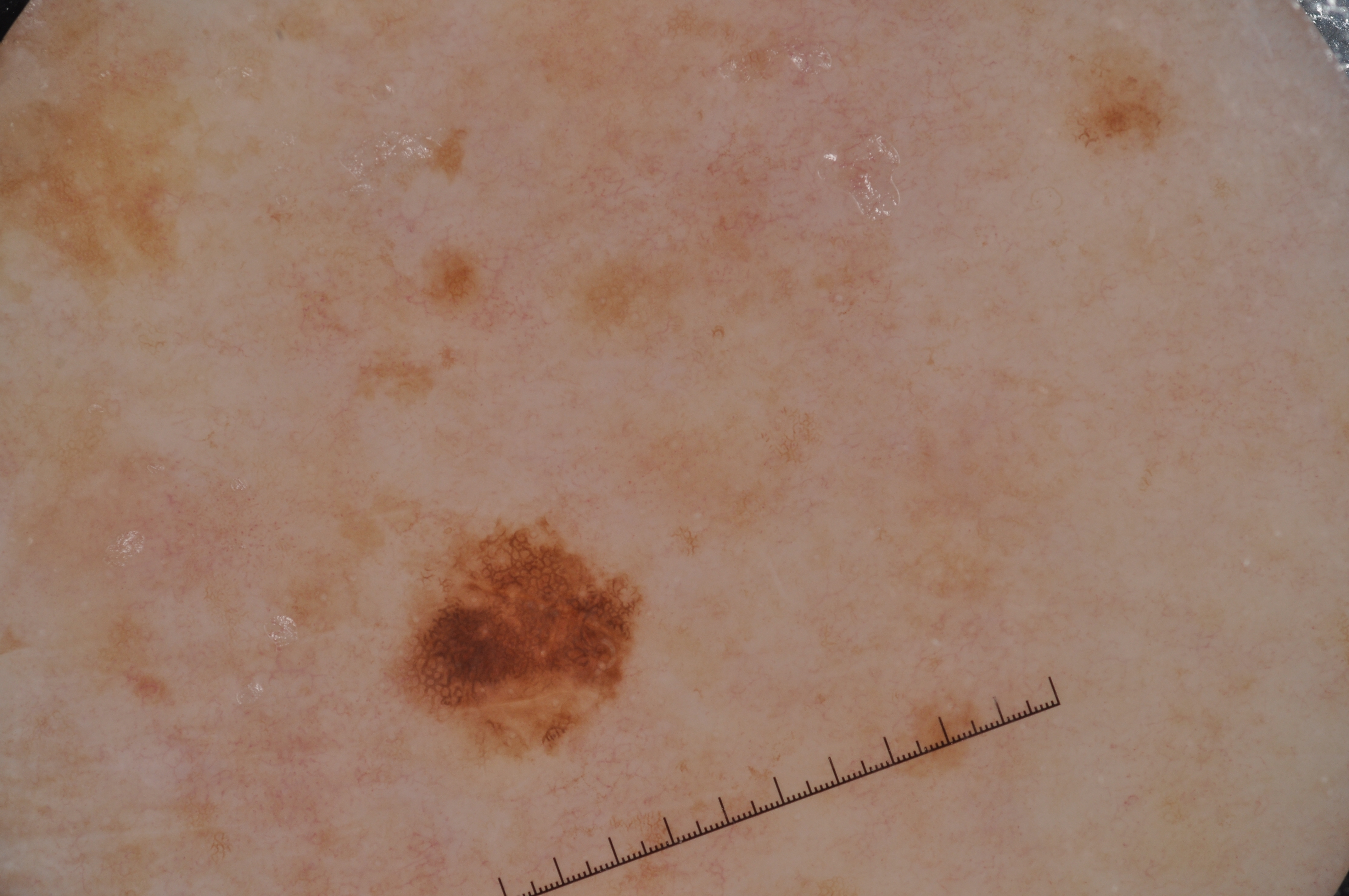Summary: A dermoscopy image of a single skin lesion. A male subject aged around 75. Dermoscopic assessment notes milia-like cysts and pigment network; no streaks or negative network. As (left, top, right, bottom), lesion location: (381, 514, 647, 763). Impression: The diagnostic assessment was a melanocytic nevus, a benign skin lesion.